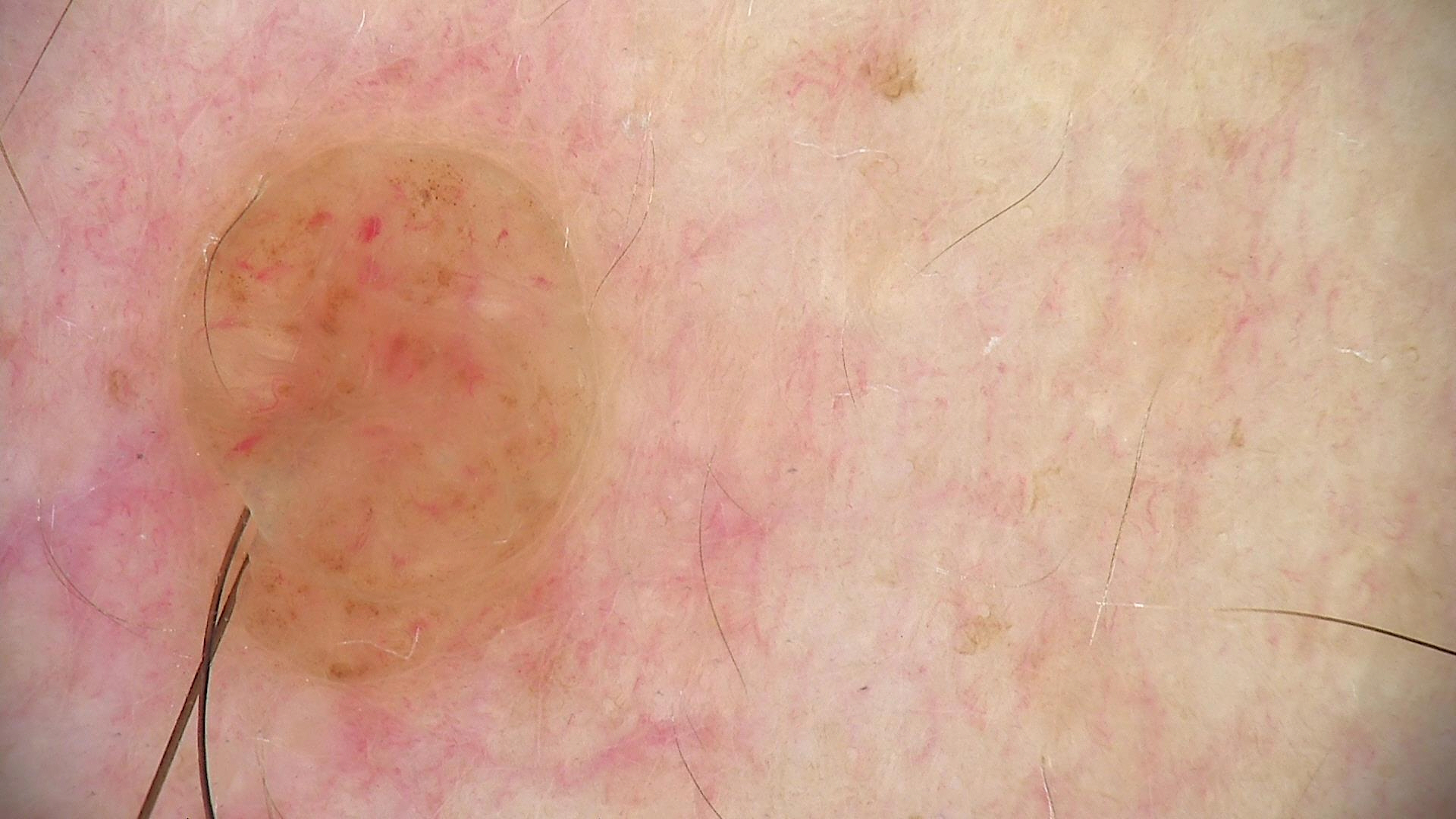| field | value |
|---|---|
| image | dermatoscopy |
| class | dermal nevus (expert consensus) |